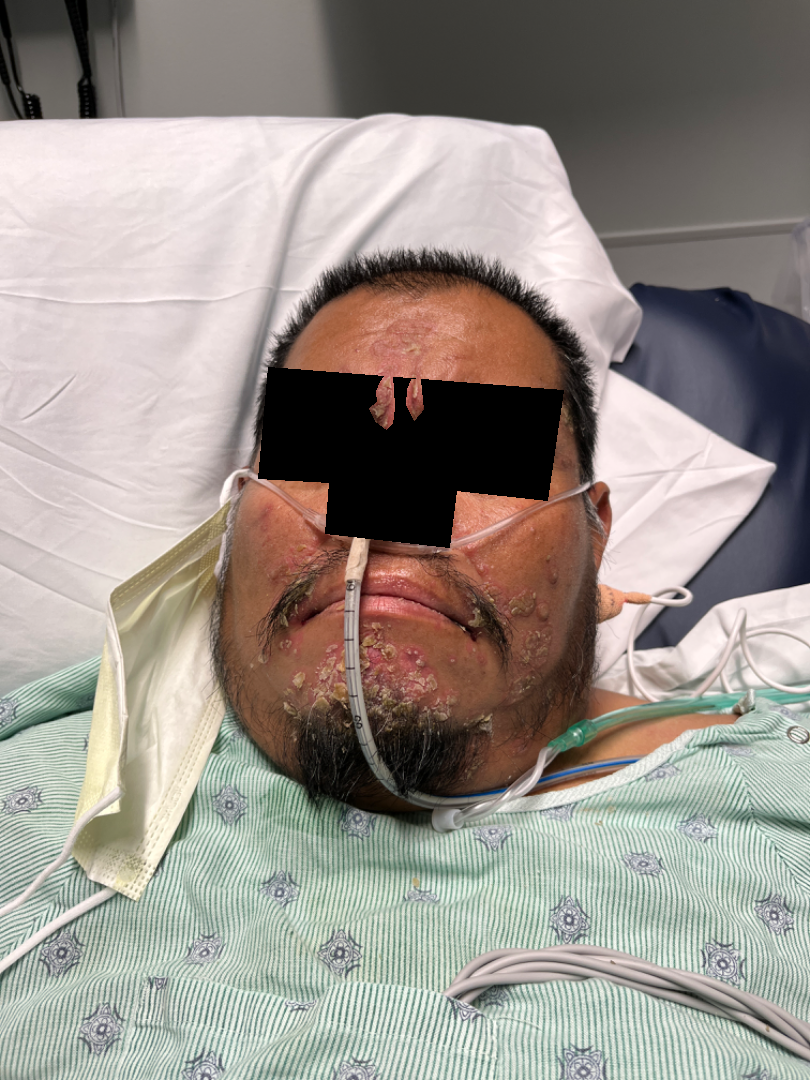The affected area is the head or neck.
The photo was captured at a distance.
Male patient, age 40–49.
A single dermatologist reviewed the case: most likely Seborrheic Dermatitis; possibly Pemphigus.